The affected area is the top or side of the foot, sole of the foot, arm, back of the torso, back of the hand and leg. An image taken at an angle: 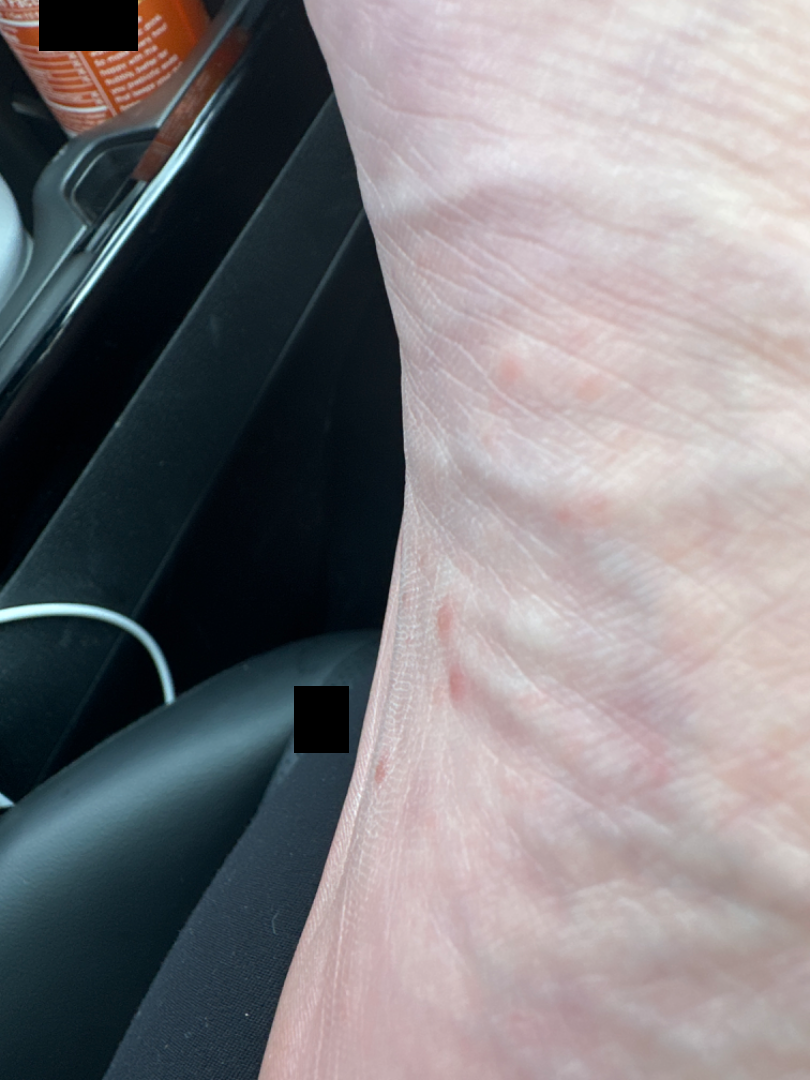Findings:
– assessment: the favored diagnosis is Insect Bite; also consider Allergic Contact Dermatitis; less probable is Urticaria